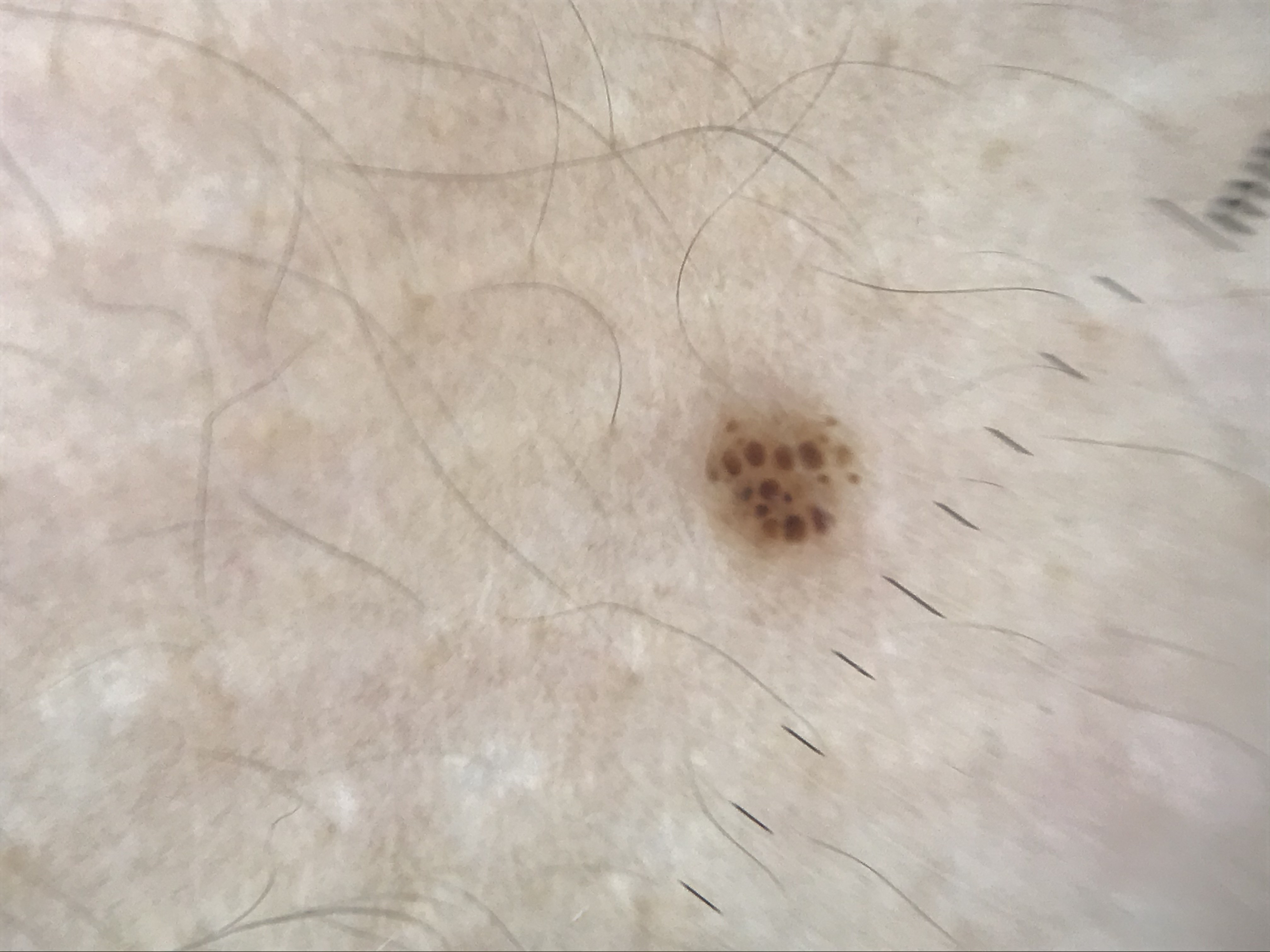{
  "diagnosis": {
    "name": "junctional nevus",
    "code": "jb",
    "malignancy": "benign",
    "super_class": "melanocytic",
    "confirmation": "expert consensus"
  }
}